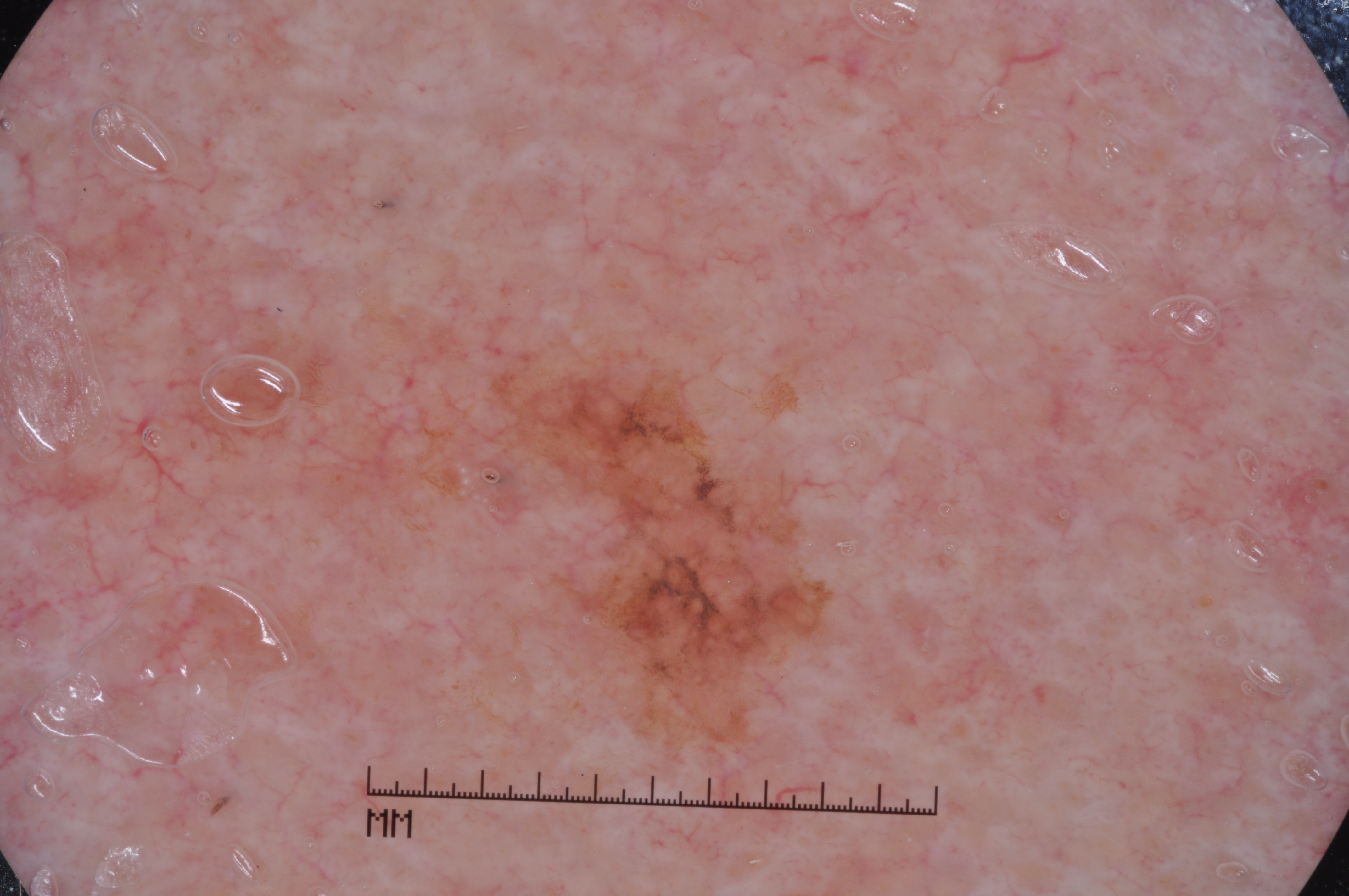A male patient, aged approximately 85 or older. A dermoscopic image of a skin lesion. The lesion is located at <bbox>517, 365, 822, 735</bbox>. Dermoscopic review identifies milia-like cysts, with no streaks, negative network, or pigment network. Histopathology confirmed a melanoma, a malignant skin lesion.